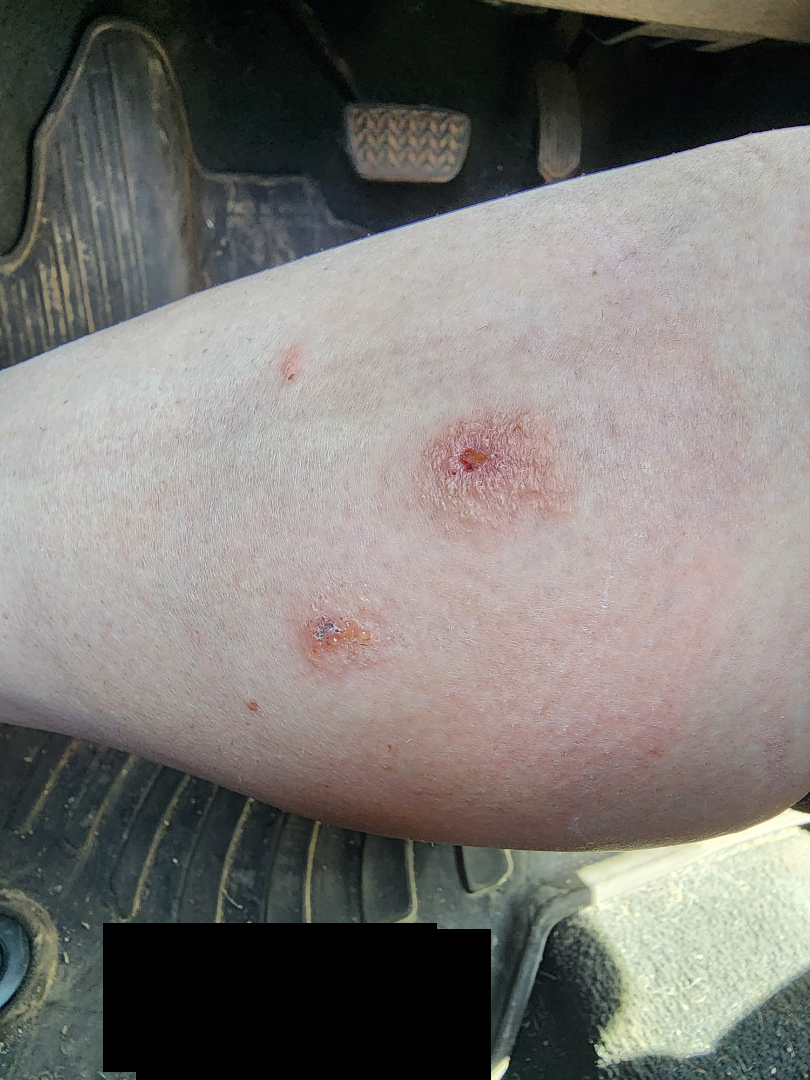{
  "duration": "one to four weeks",
  "skin_tone": {
    "monk_skin_tone": 2
  },
  "body_site": "leg",
  "shot_type": "close-up",
  "symptoms": [
    "bleeding",
    "itching"
  ],
  "differential": {
    "leading": [
      "Eczema"
    ]
  }
}